This is a close-up image: 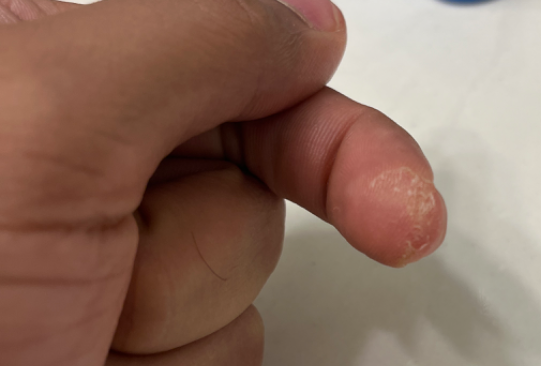skin tone = Fitzpatrick IV; non-clinician graders estimated MST 6 (US pool) or 4 (India pool) | diagnostic considerations = Verruca vulgaris (possible); Eczema (possible); Hyperkeratosis of skin (possible).